No relevant lesion symptoms reported; texture is reported as flat; reported duration is about one day; a close-up photograph; located on the arm — 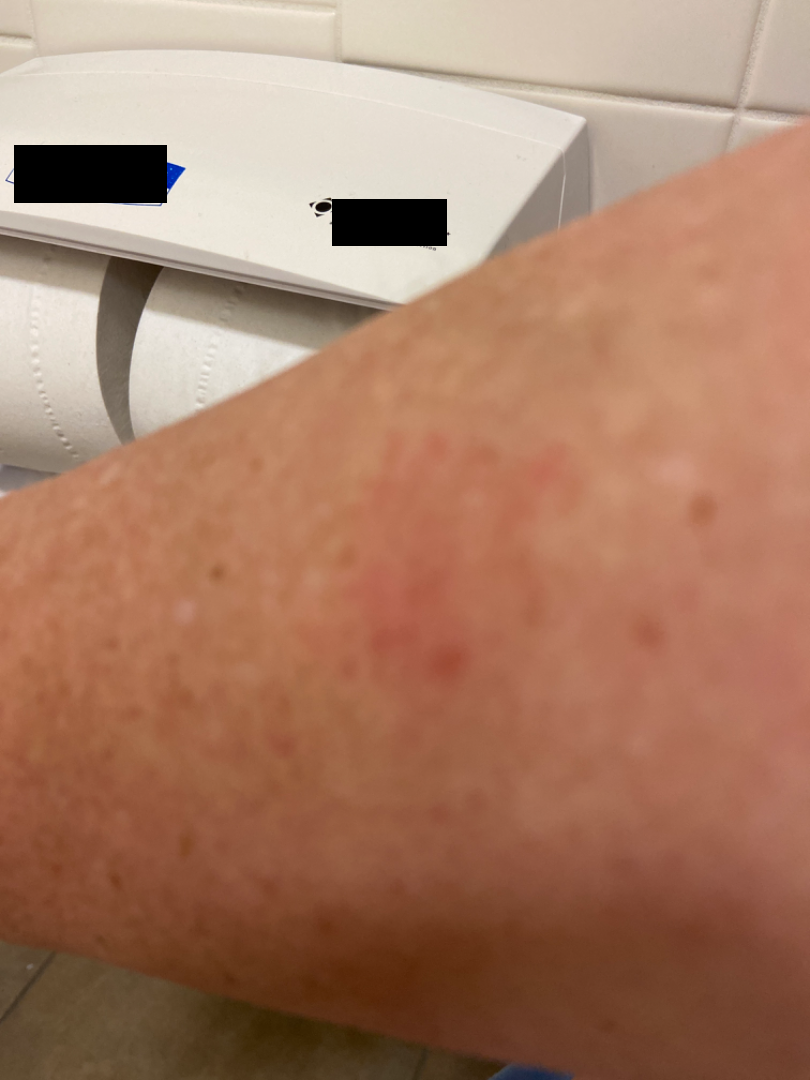The skin condition could not be confidently assessed from this image.